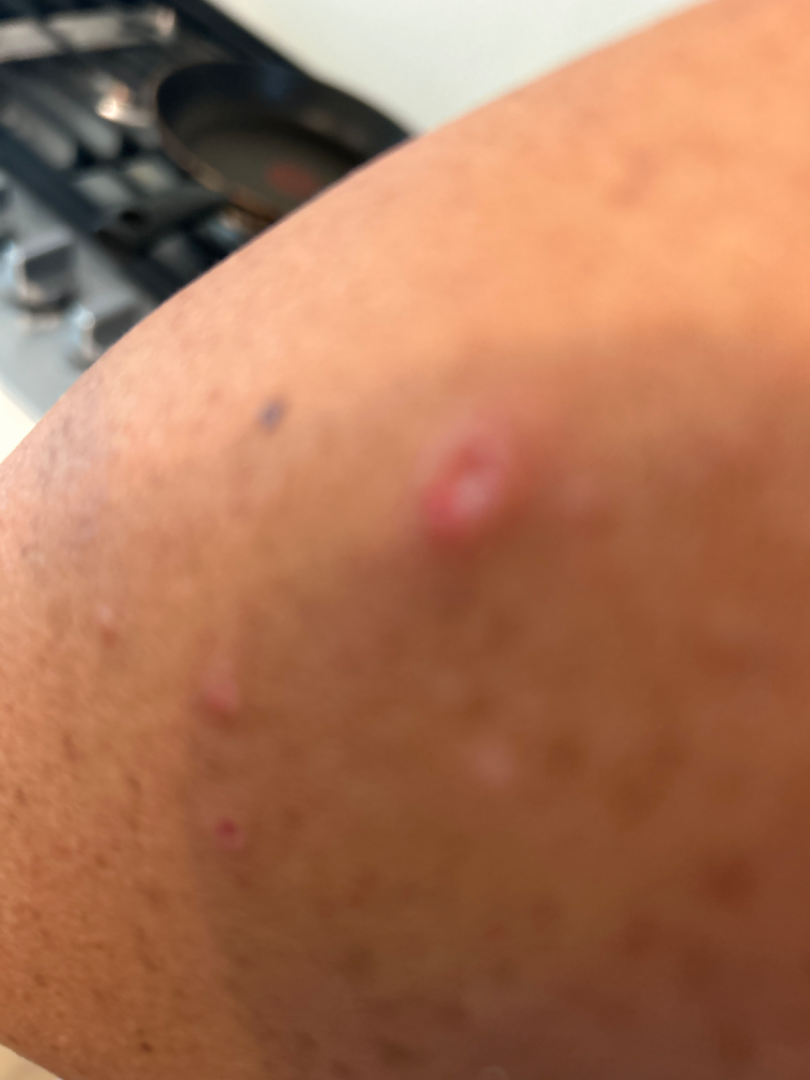Impression:
The condition could not be reliably identified from the image.
History:
The photograph was taken at an angle. The affected area is the head or neck and front of the torso.